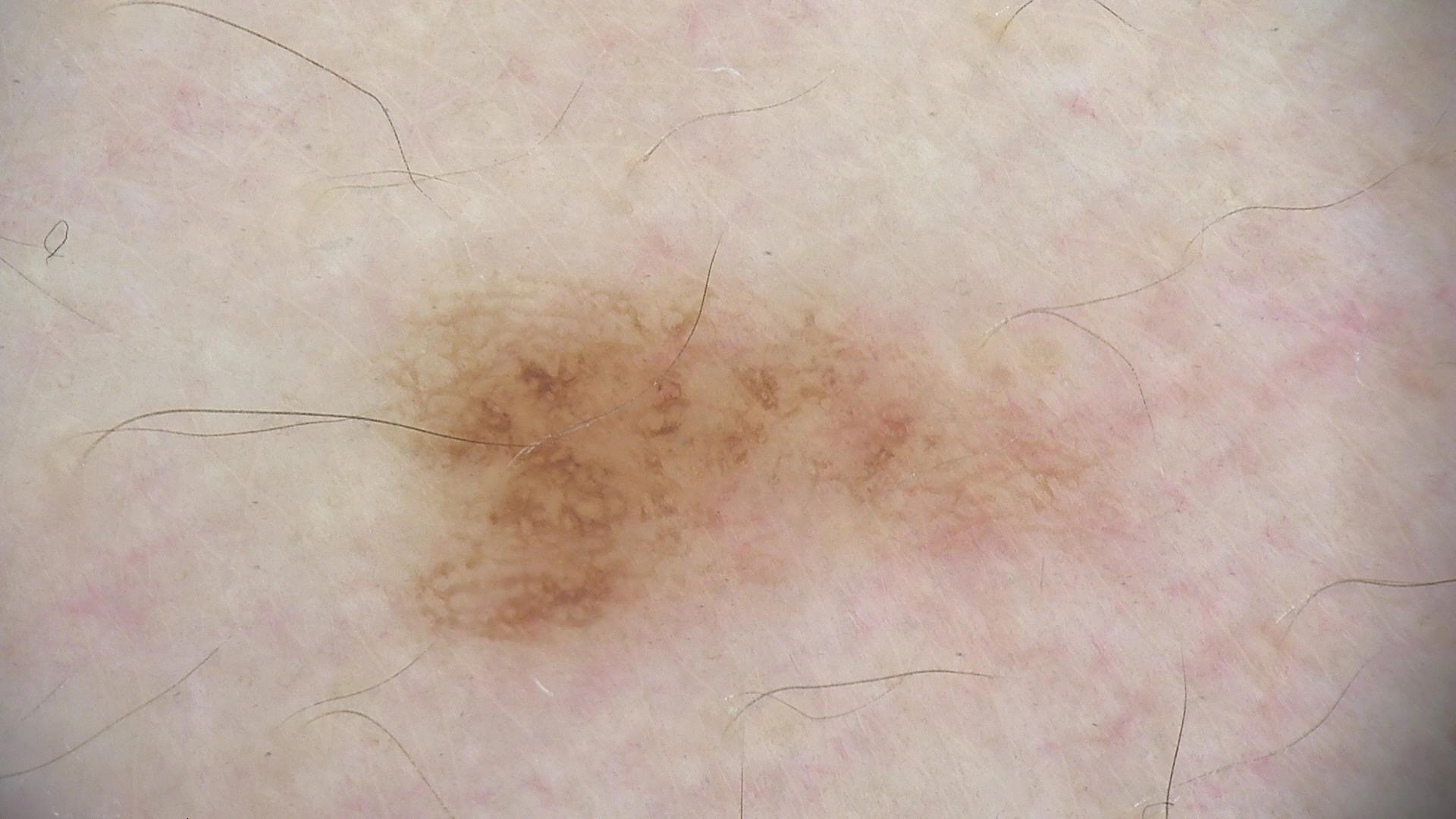Conclusion: Classified as a dysplastic junctional nevus.